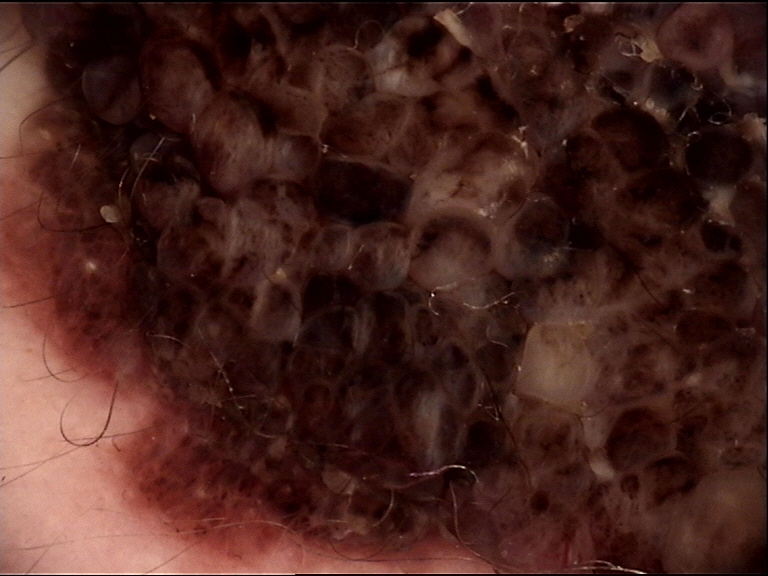Consistent with a congenital compound nevus.